A clinical close-up photograph of a skin lesion · a patient in their 80s: 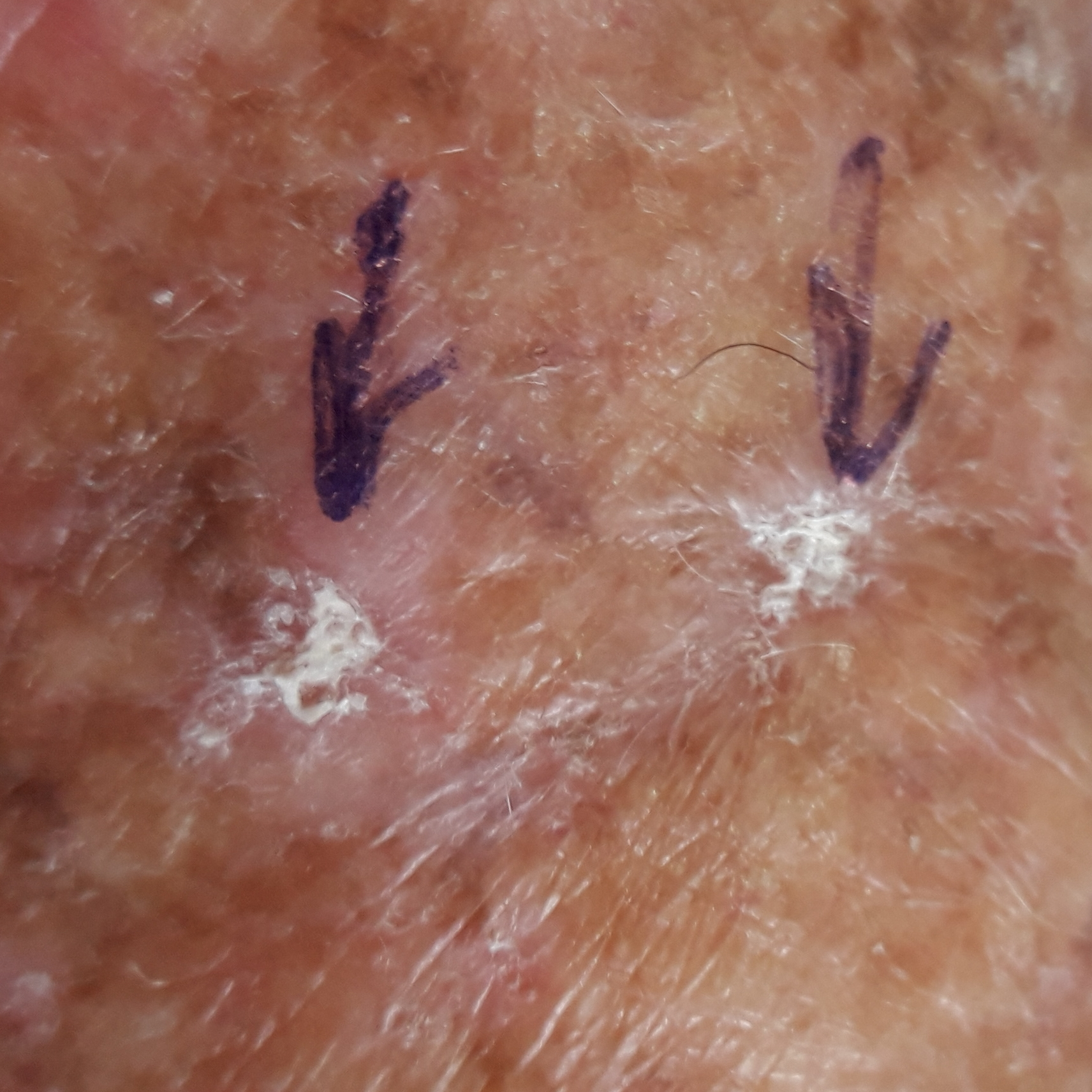The lesion was found on an arm.
By the patient's account, the lesion itches, but has not grown and does not hurt.
The consensus clinical diagnosis was a lesion with uncertain malignant potential — an actinic keratosis.